The photograph was taken at a distance:
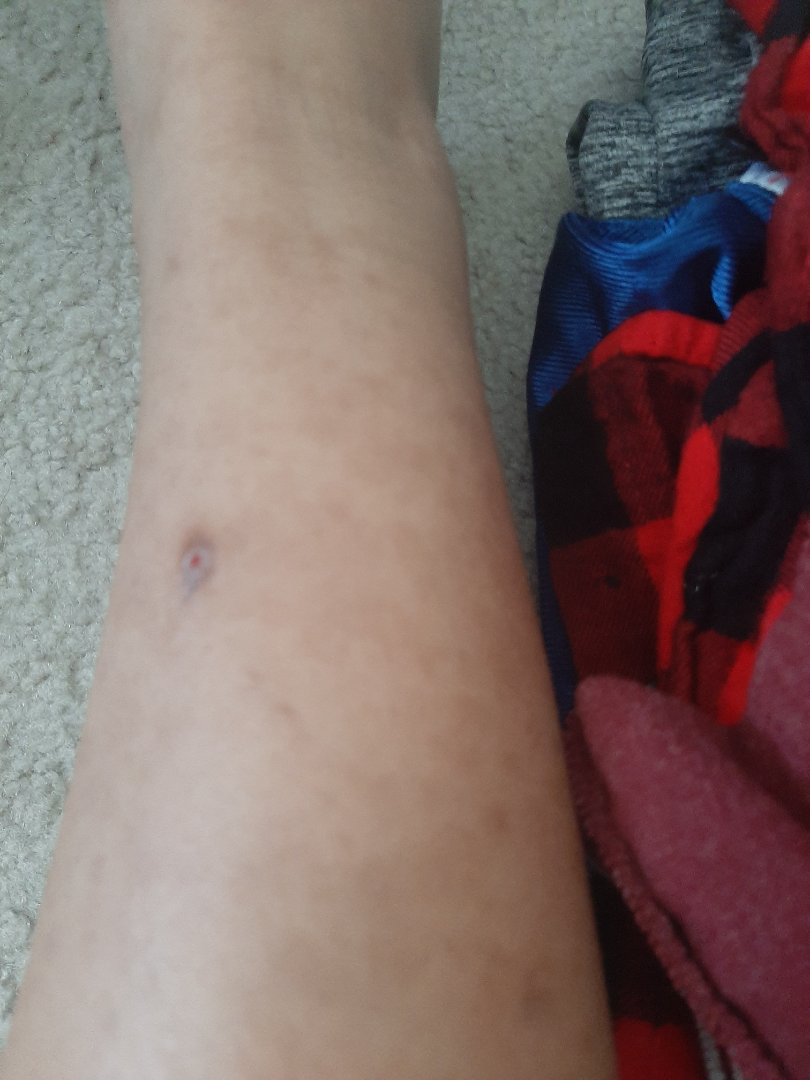Review:
No differential diagnosis could be assigned on photographic review.